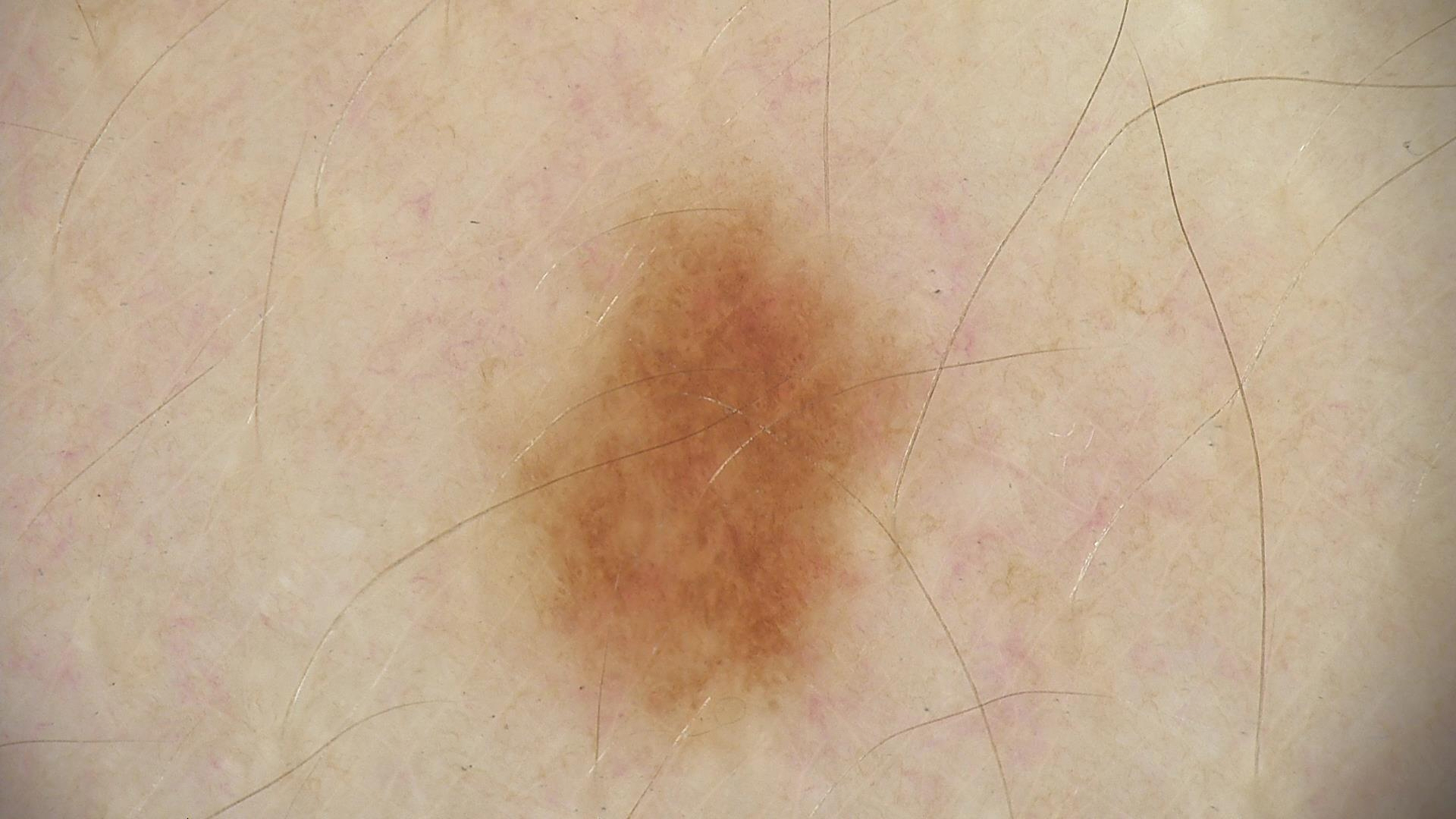A dermatoscopic image of a skin lesion. Classified as a benign lesion — a dysplastic junctional nevus.